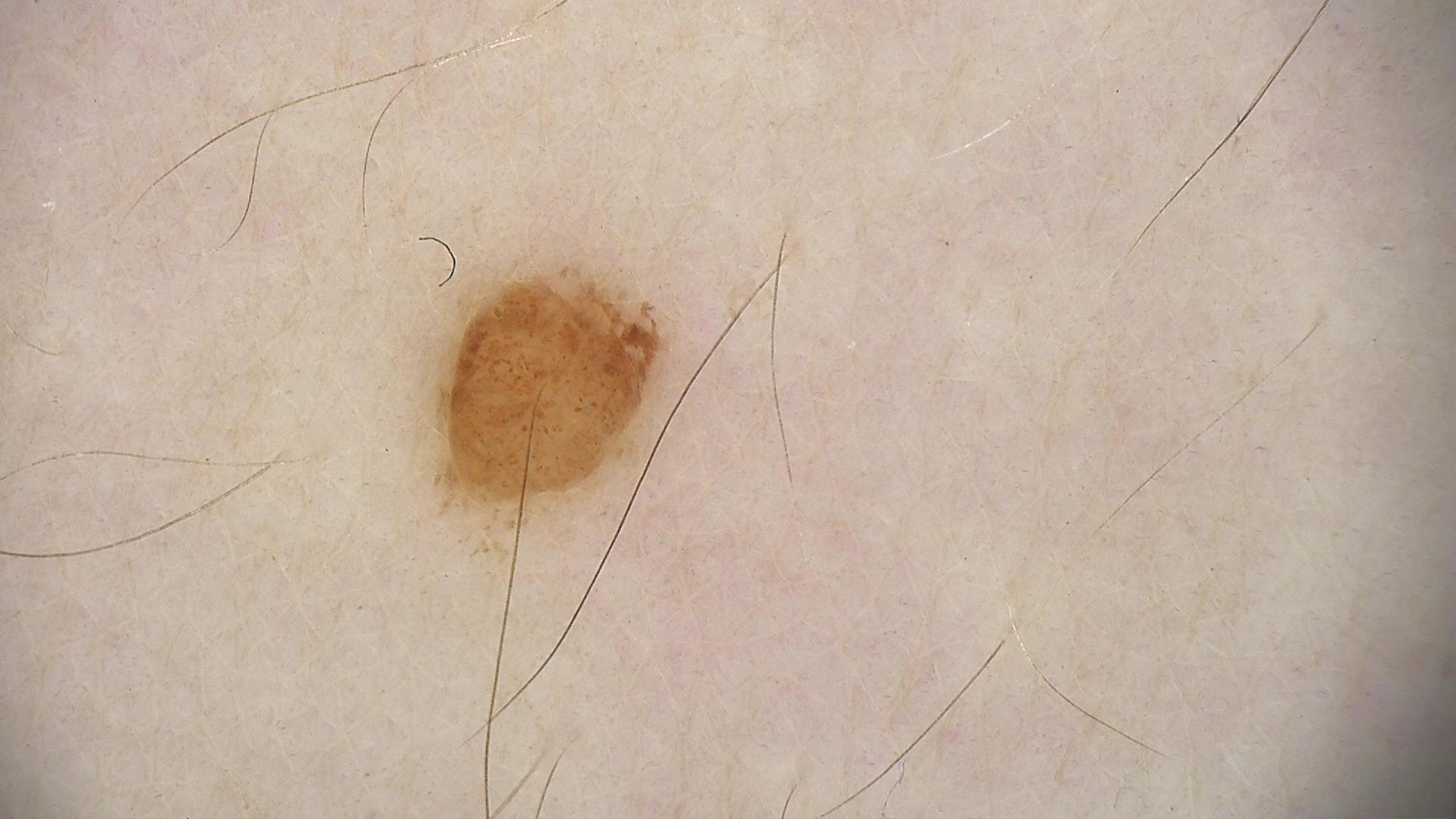A skin lesion imaged with a dermatoscope. The architecture is that of a banal lesion. Classified as a compound nevus.